Located on the arm, back of the hand, leg, back of the torso and head or neck · female contributor, age 30–39 · symptoms reported: itching, burning, enlargement and pain · the patient reports the lesion is raised or bumpy and flat · reported duration is less than one week · close-up view · the patient considered this skin that appeared healthy to them · the patient also reports fatigue — 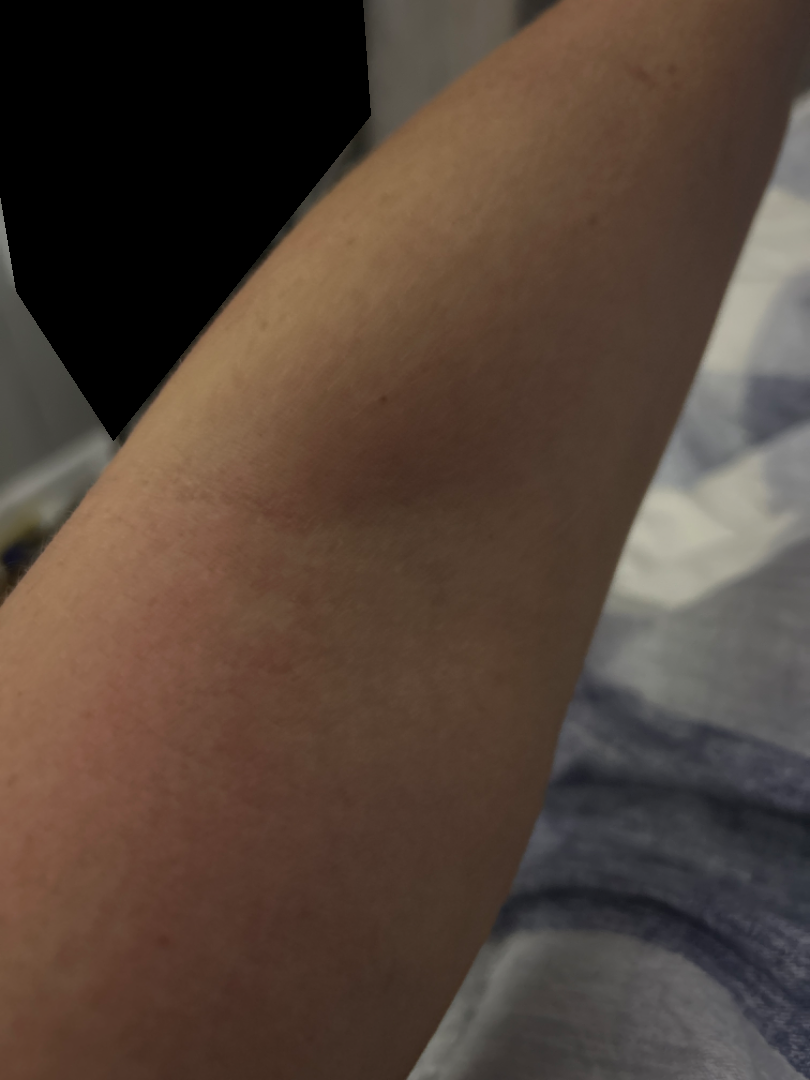Three dermatologists each reviewed the case: the differential is split between Irritant Contact Dermatitis and Allergic Contact Dermatitis; an alternative is Eczema.